The contributor reports the lesion is flat; self-categorized by the patient as a rash; no constitutional symptoms were reported; the affected area is the top or side of the foot; symptoms reported: itching; a close-up photograph; the contributor reports the condition has been present for one to four weeks.
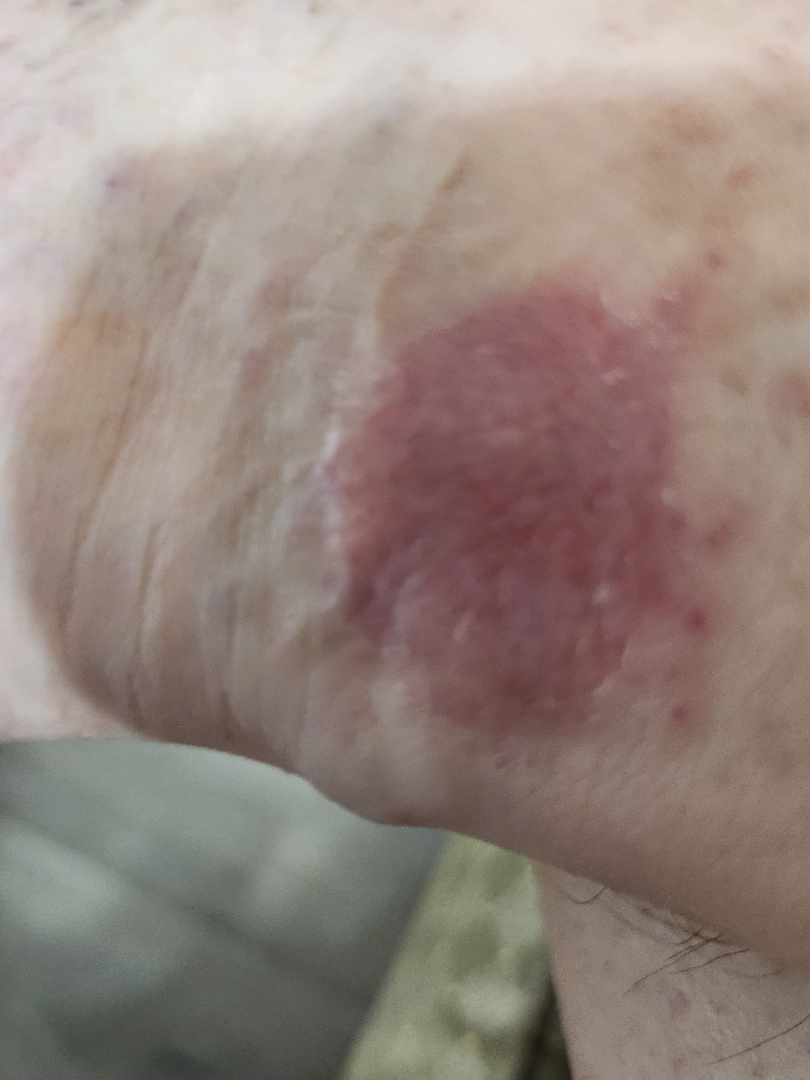Impression: Favoring Eczema; with consideration of Psoriasis; less probable is Drug Rash.